A dermoscopic close-up of a skin lesion: 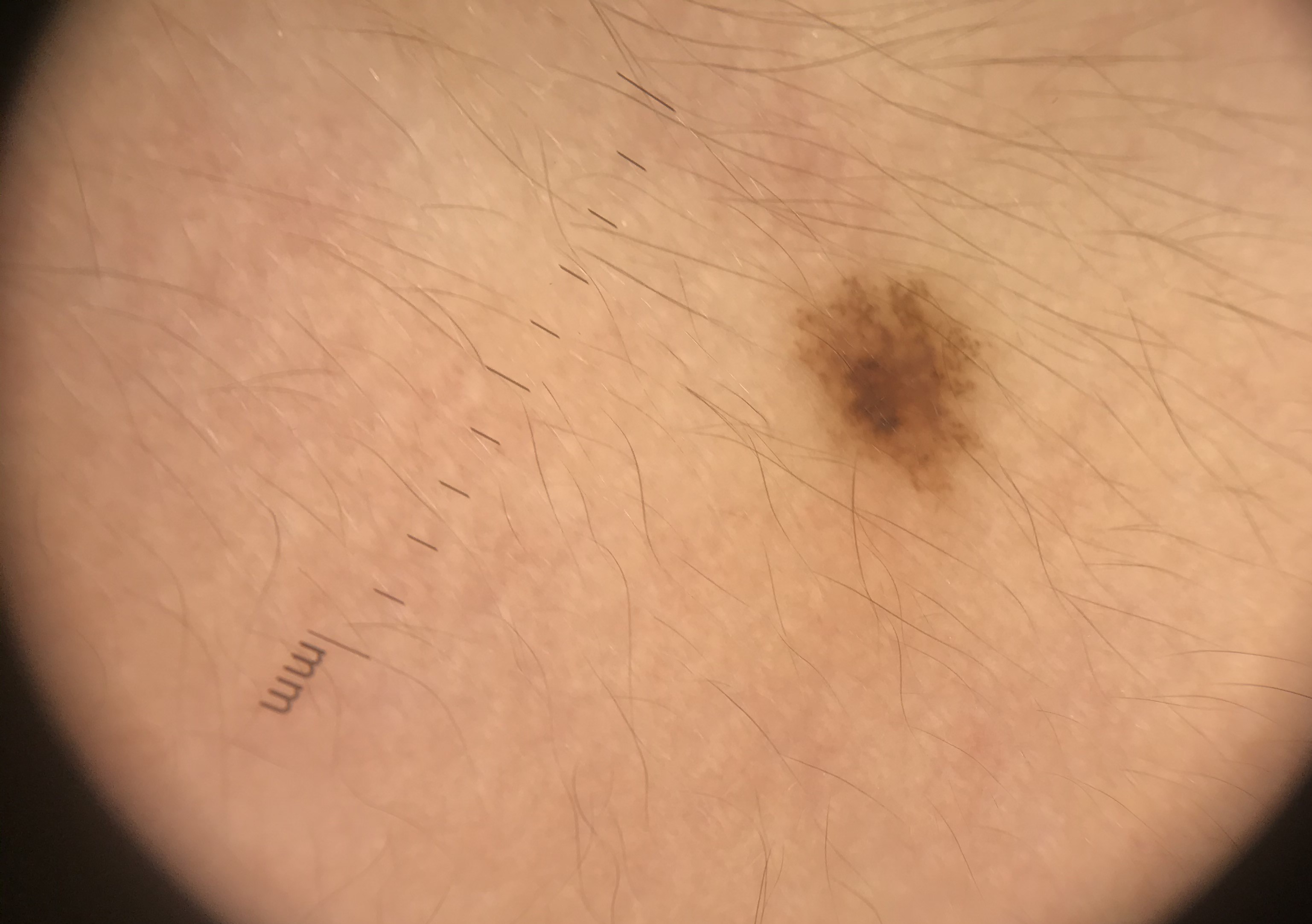Labeled as a dysplastic junctional nevus.